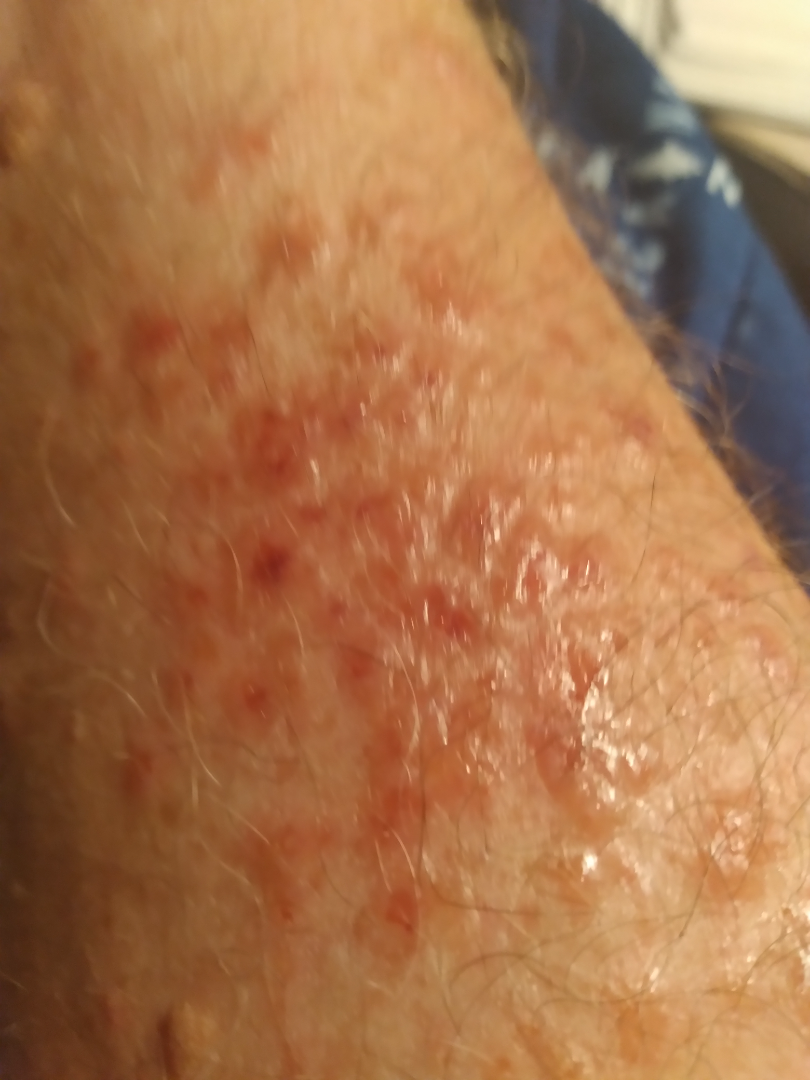Case summary:
- view · close-up
- lesion texture · raised or bumpy and fluid-filled
- assessment · Tinea (possible); Eczema (possible); Allergic Contact Dermatitis (possible)